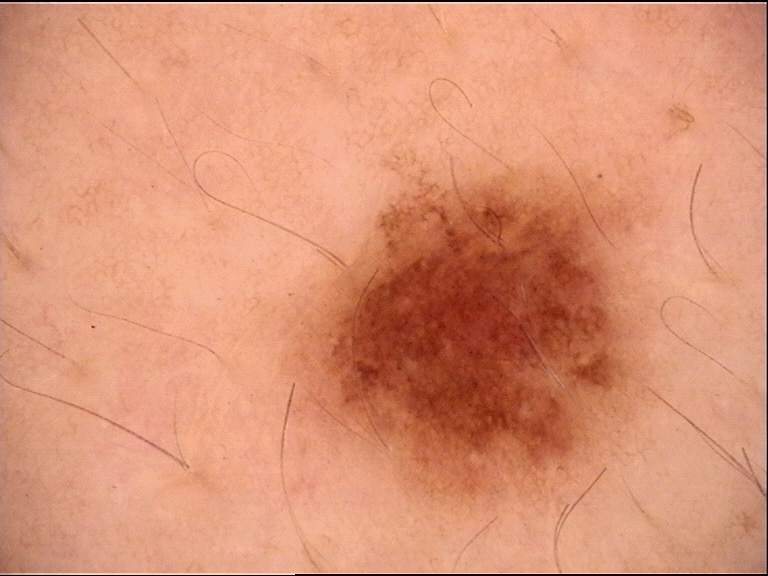image=dermatoscopy; diagnosis=dysplastic junctional nevus (expert consensus).